Close-up view: 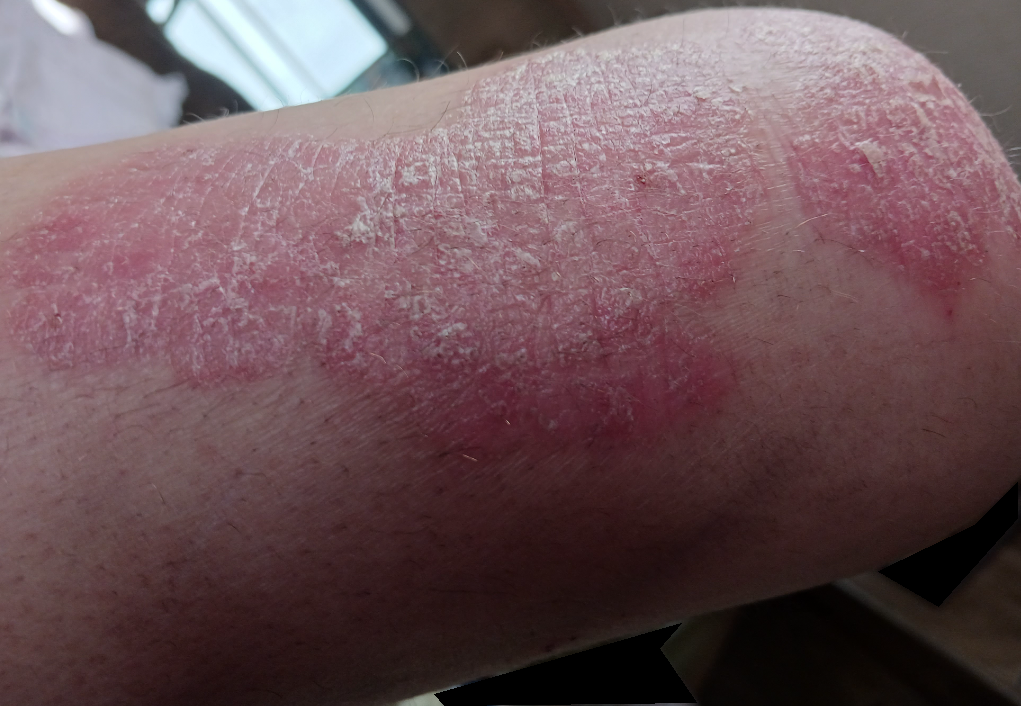* clinical impression: most consistent with Psoriasis